A skin lesion imaged with a dermatoscope.
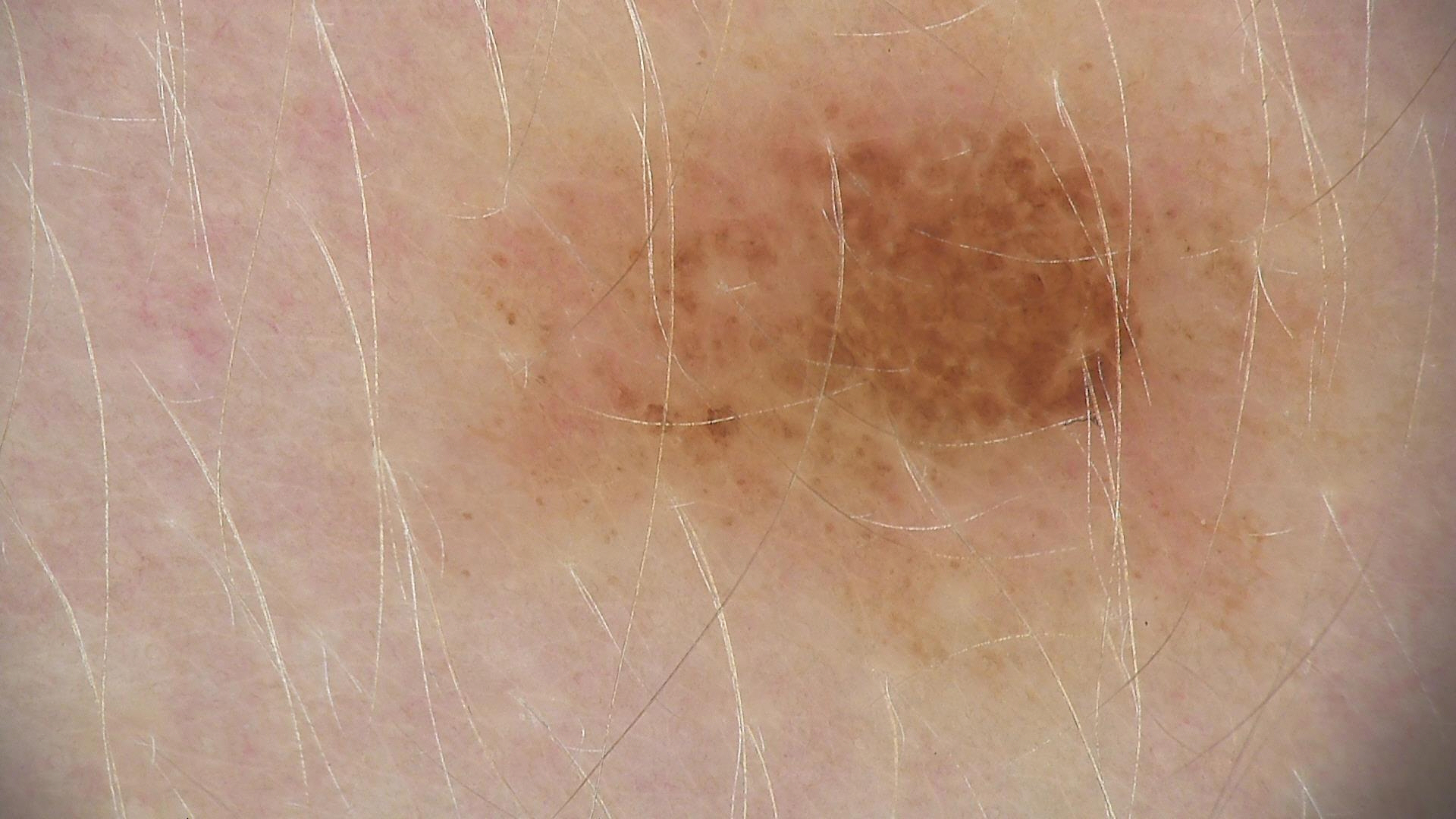label=dysplastic junctional nevus (expert consensus).